The patient considered this a rash. A close-up photograph. Female patient, age 30–39. The lesion is described as fluid-filled, rough or flaky and raised or bumpy. The lesion is associated with bothersome appearance, itching and burning. The lesion involves the arm — 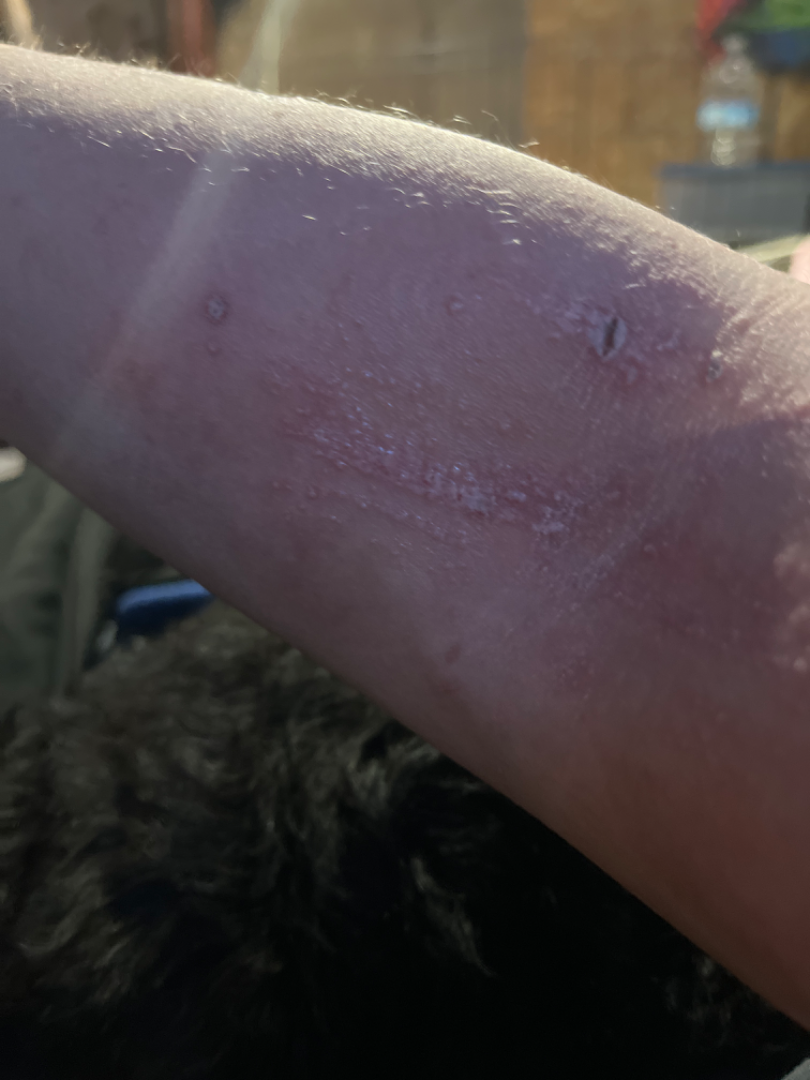<case>
  <differential>
    <tied_lead>Psoriasis, Eczema, Lichen Simplex Chronicus</tied_lead>
  </differential>
</case>